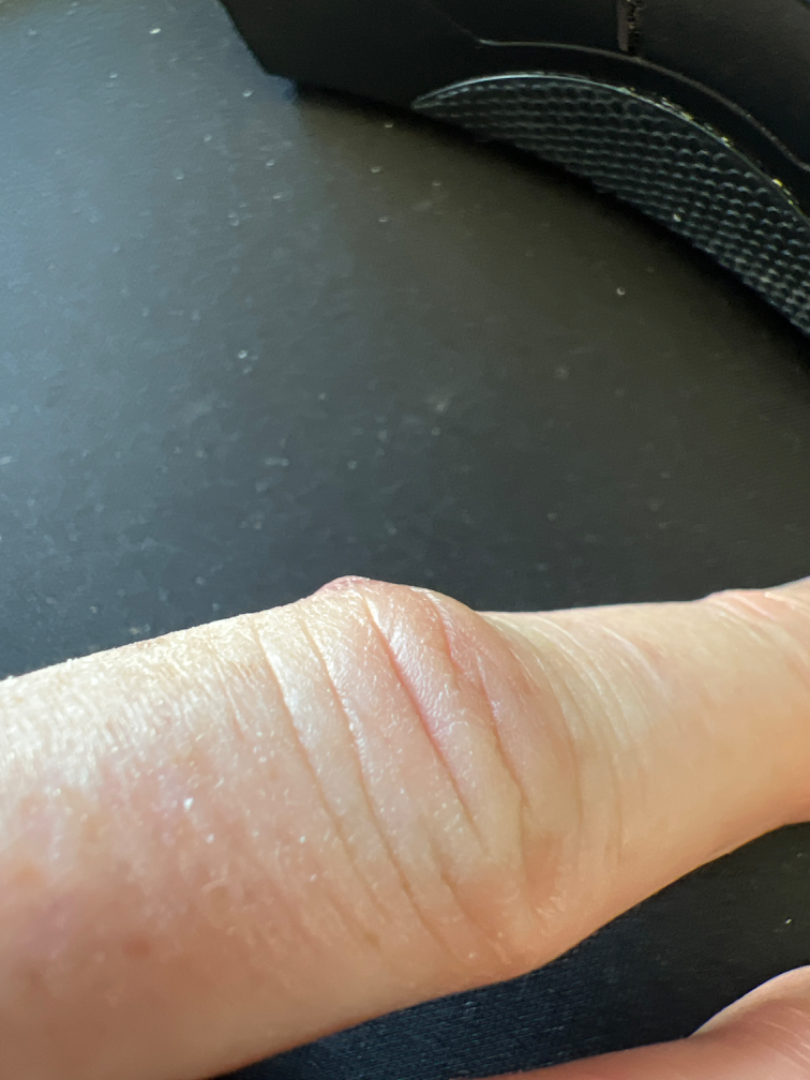framing = at an angle
surface texture = fluid-filled
affected area = back of the hand
skin tone = FST I
symptom duration = about one day
patient describes the issue as = a rash
subject = female
other reported symptoms = none reported
diagnostic considerations = Impetigo, Chilblain and Leukocytoclastic Vasculitis were considered with similar weight